A dermoscopy image of a single skin lesion.
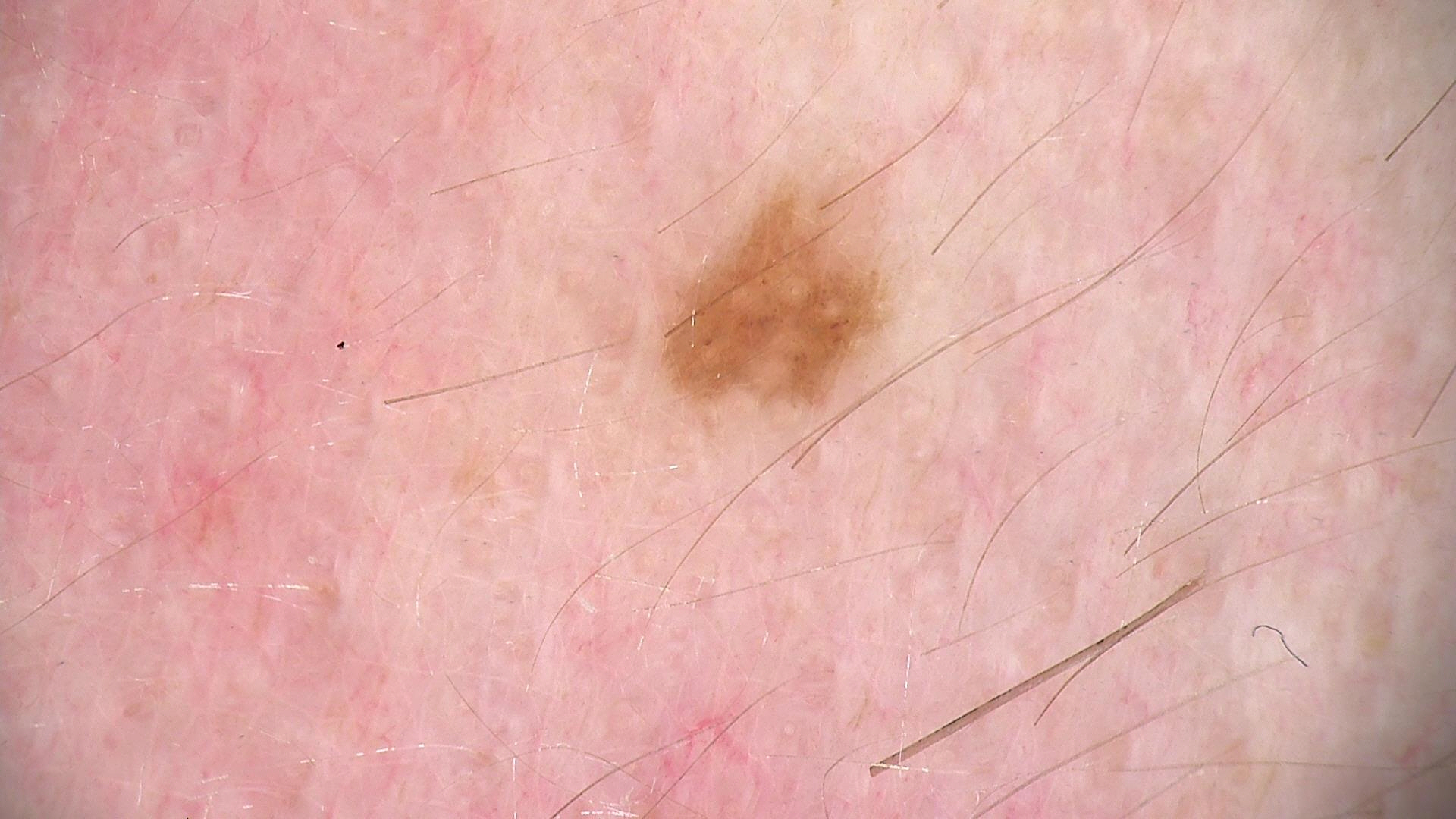The diagnosis was a dysplastic junctional nevus.